Fitzpatrick skin type I; non-clinician graders estimated Monk Skin Tone 2. The photo was captured at a distance — 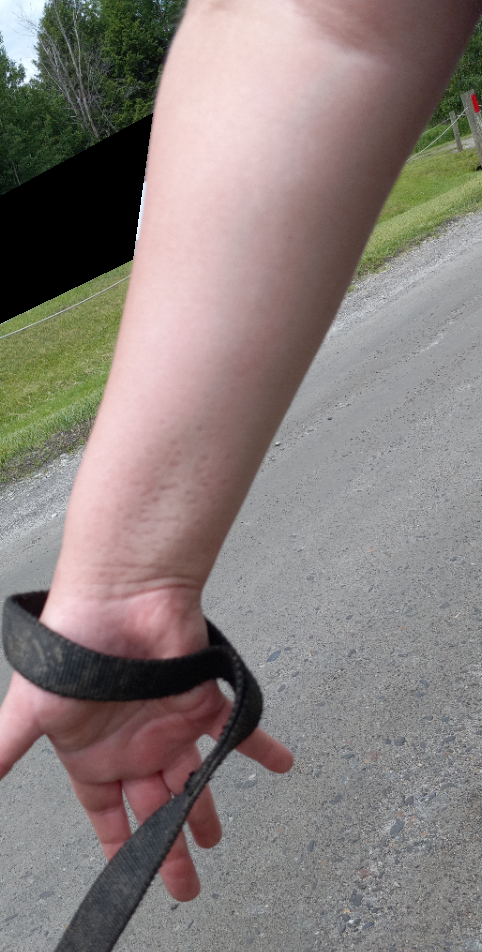The skin findings could not be characterized from the image.